A male subject 83 years old · the patient says their skin reddens with sun exposure — 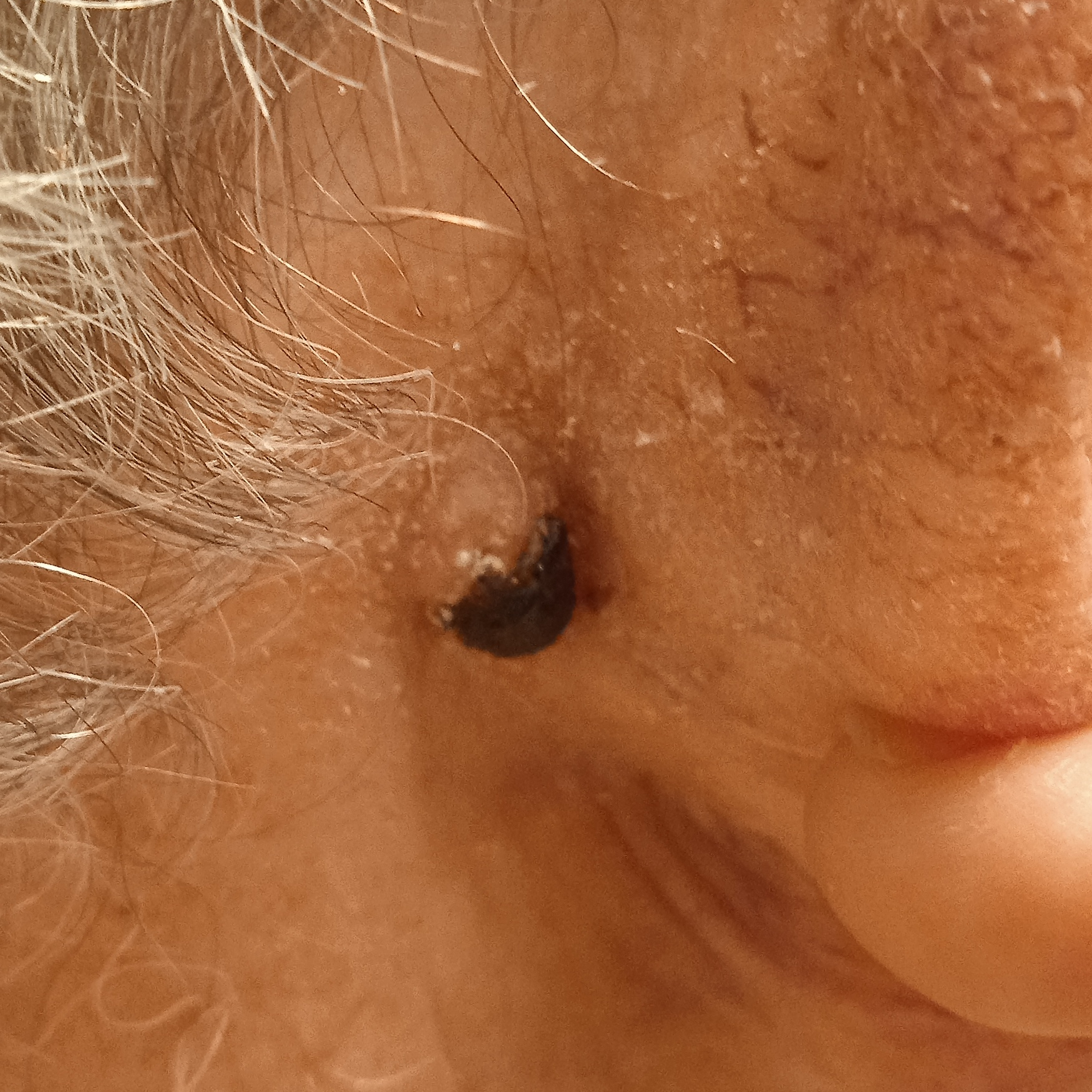Located on the head.
The lesion is about 8 mm across.
The biopsy diagnosis was a basal cell carcinoma, following excision, with a measured tumor thickness of 2.7 mm.